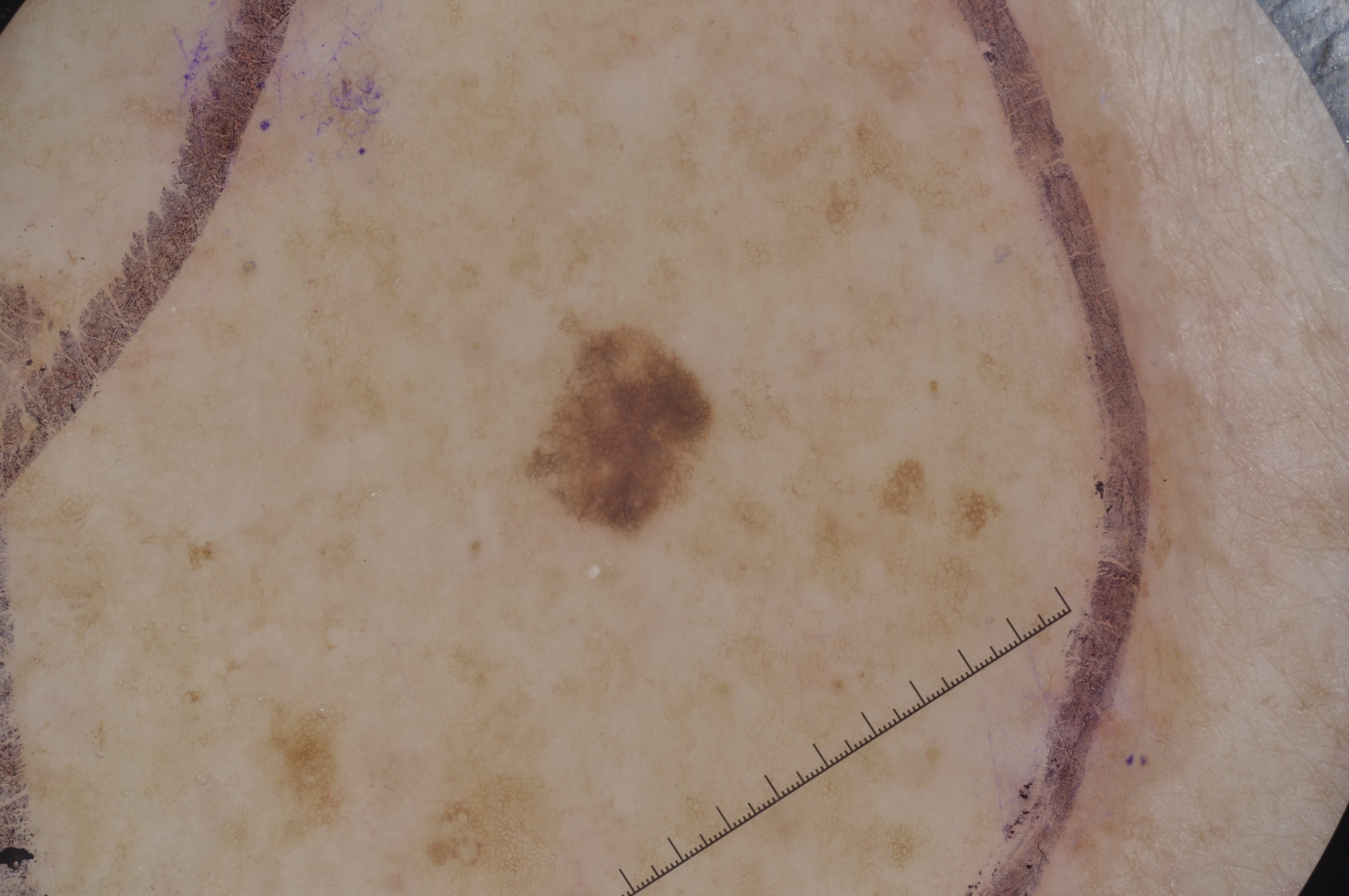Dermoscopy of a skin lesion. A male subject, about 70 years old. A small lesion occupying a minor part of the field. Dermoscopic examination shows pigment network. With coordinates (x1, y1, x2, y2), lesion location: (538, 329, 706, 525). Diagnosed as a melanocytic nevus, a benign lesion.